Female subject, age 50–59 · located on the head or neck · the photograph is a close-up of the affected area: 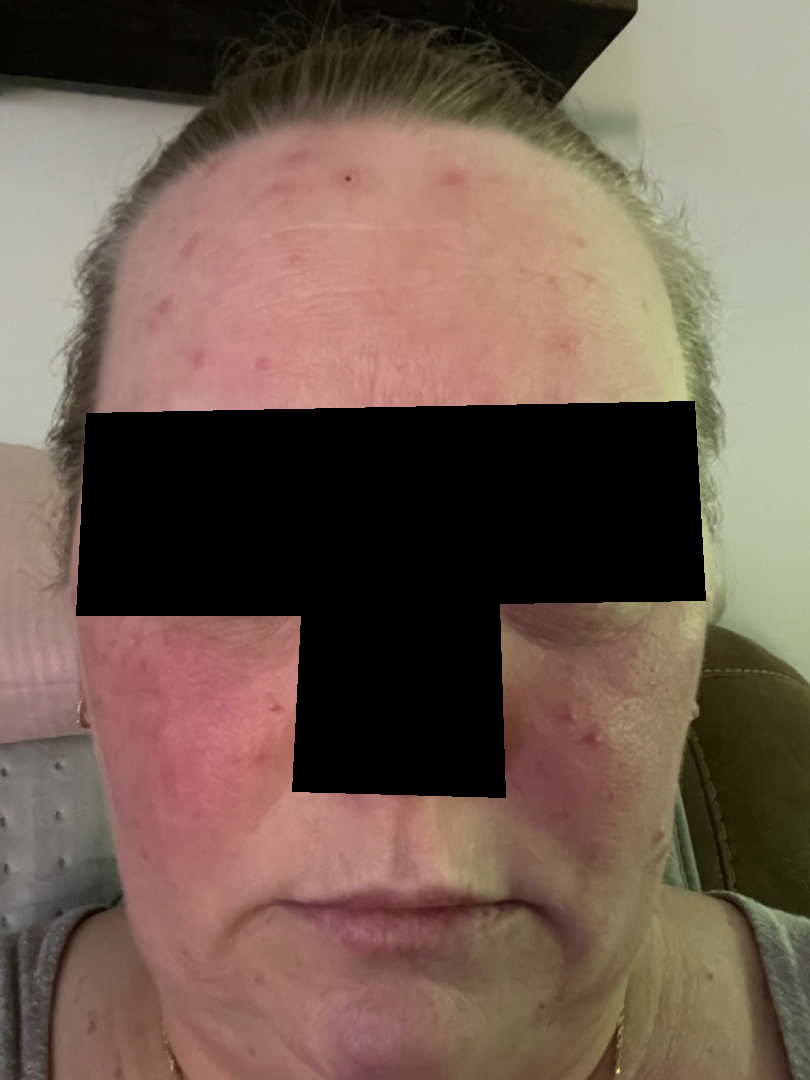assessment = the impression is Rosacea.